A skin lesion imaged with a dermatoscope:
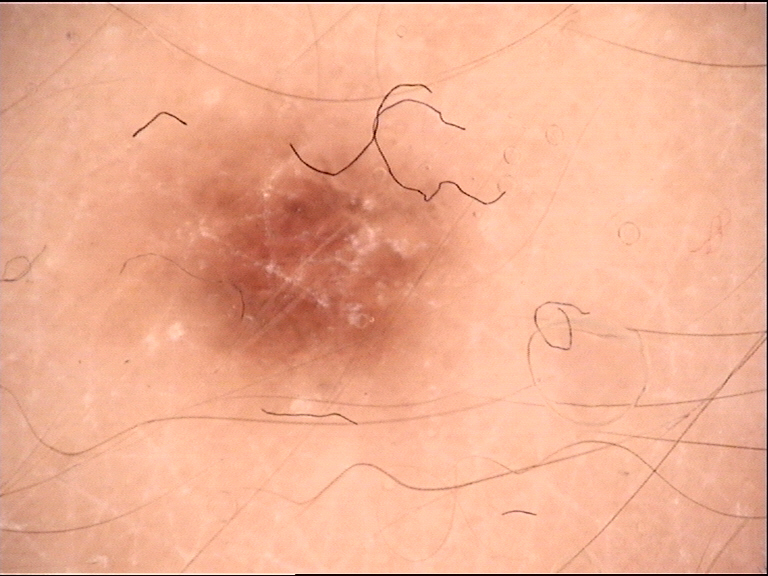category: fibro-histiocytic; class: dermatofibroma (expert consensus).